A dermoscopy image of a single skin lesion:
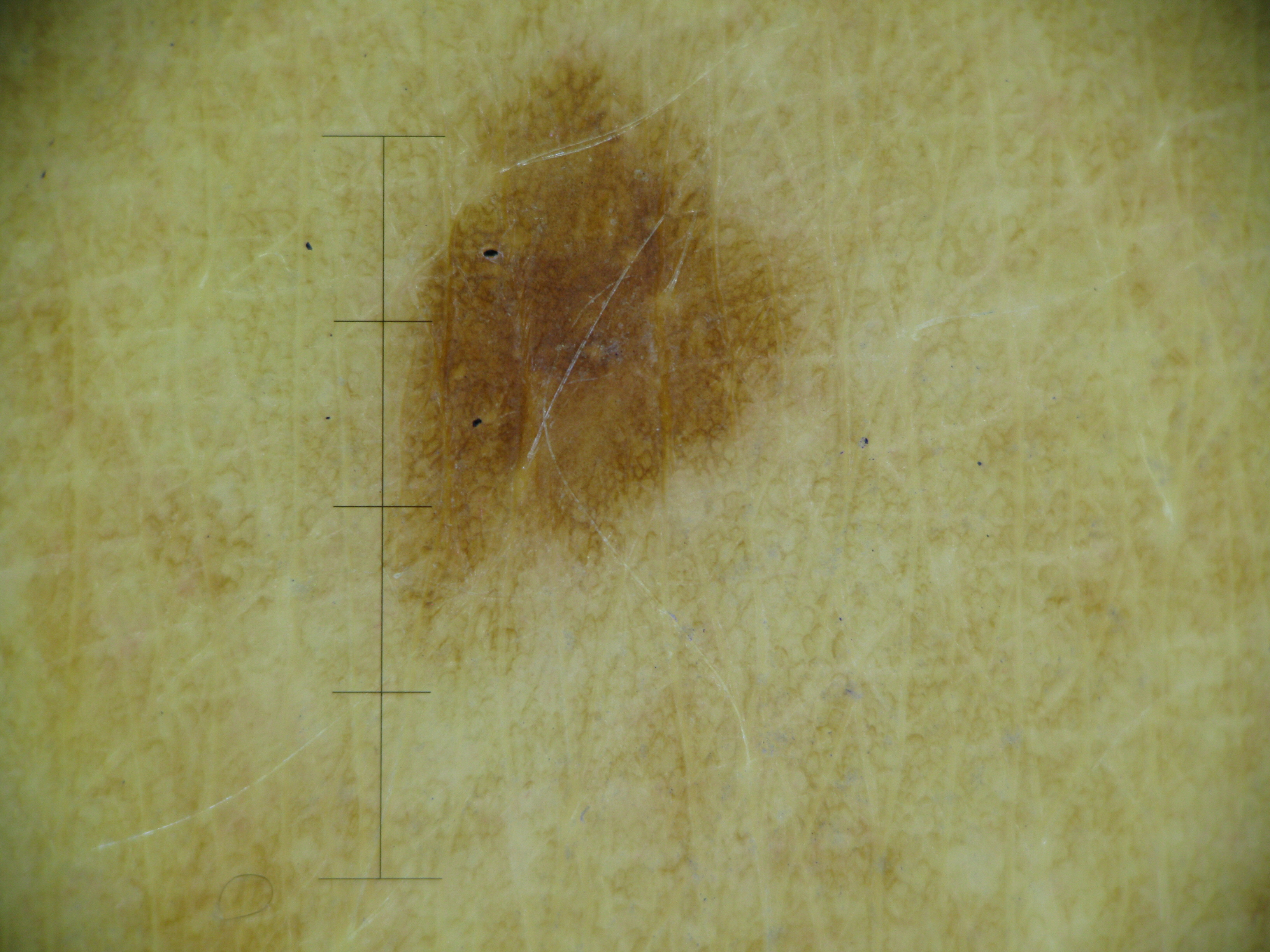Impression:
Labeled as a banal lesion — a junctional nevus.